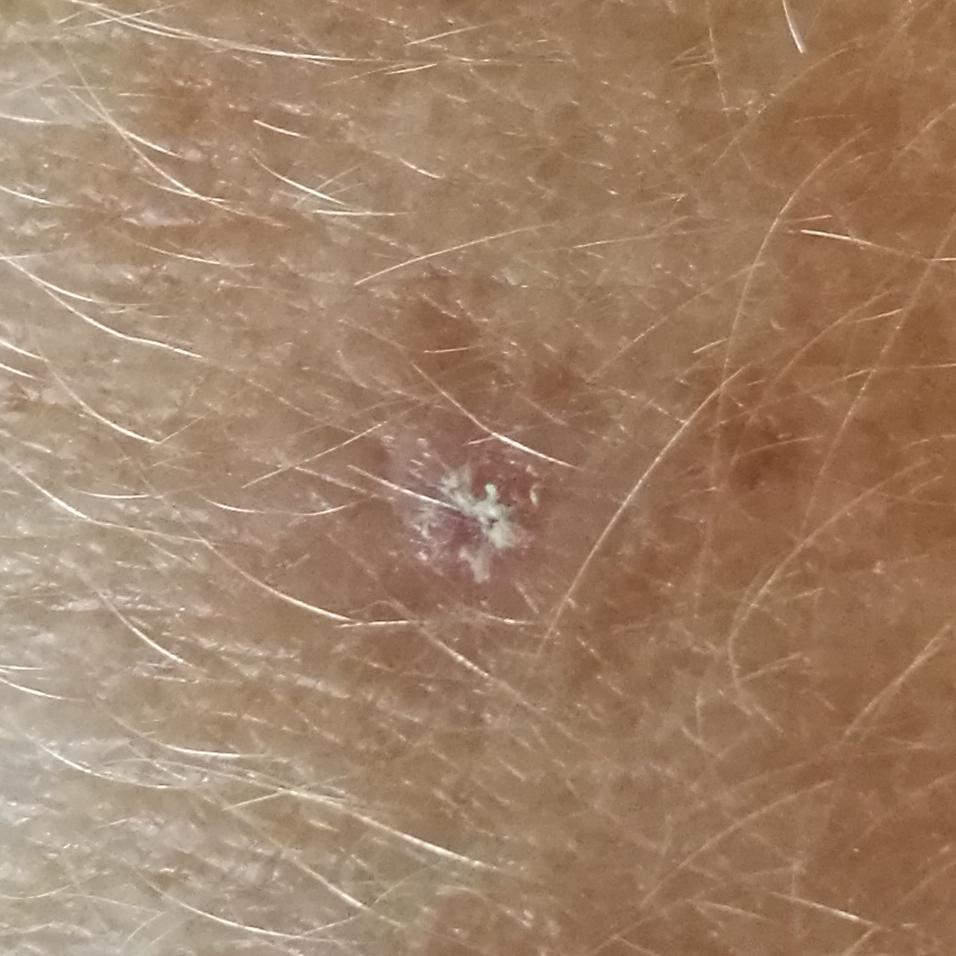Notes:
• patient · aged 51
• imaging · clinical photograph
• body site · a forearm
• patient-reported symptoms · itching
• diagnostic label · actinic keratosis (clinical consensus)